The contributor is a male aged 18–29; located on the front of the torso; close-up view — 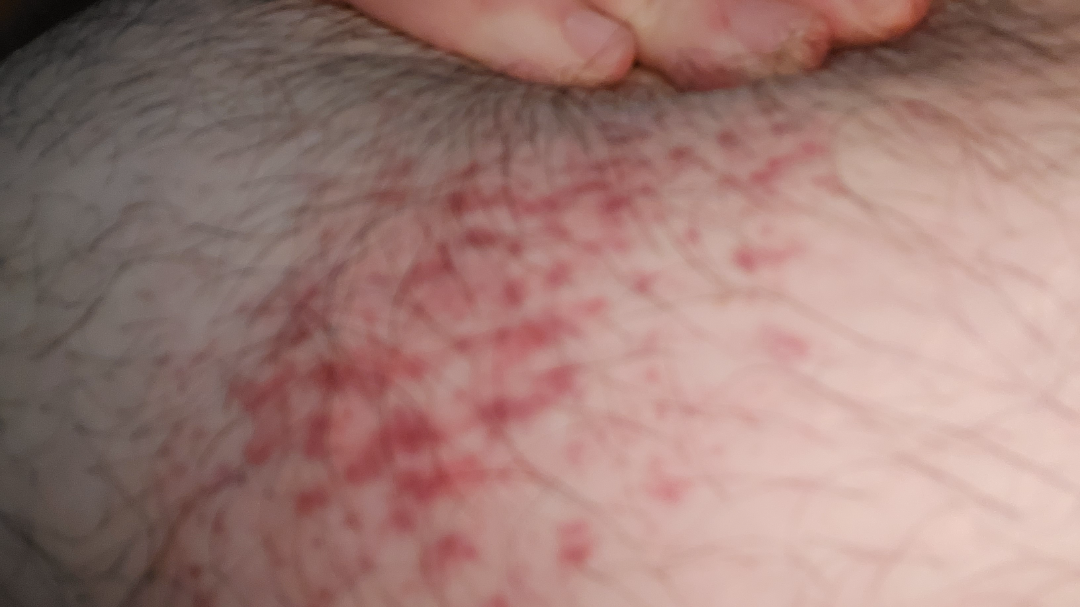{"assessment": "unable to determine"}